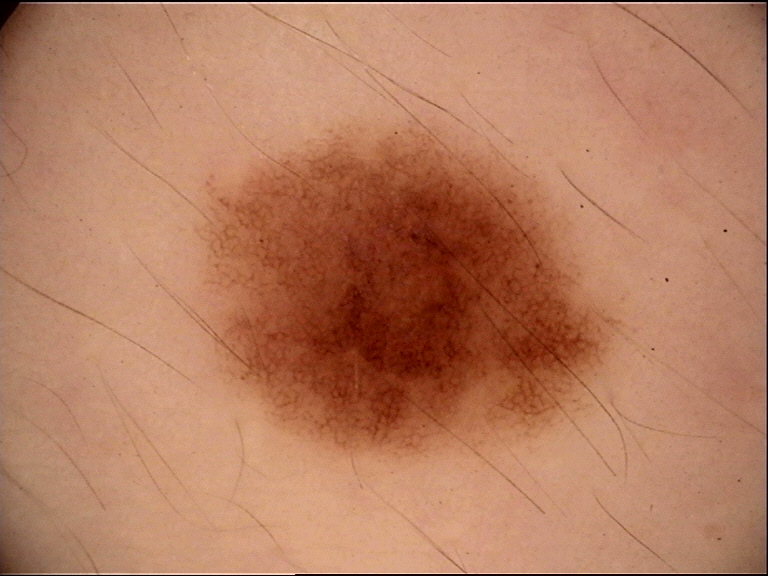Classified as a benign lesion — a dysplastic junctional nevus.